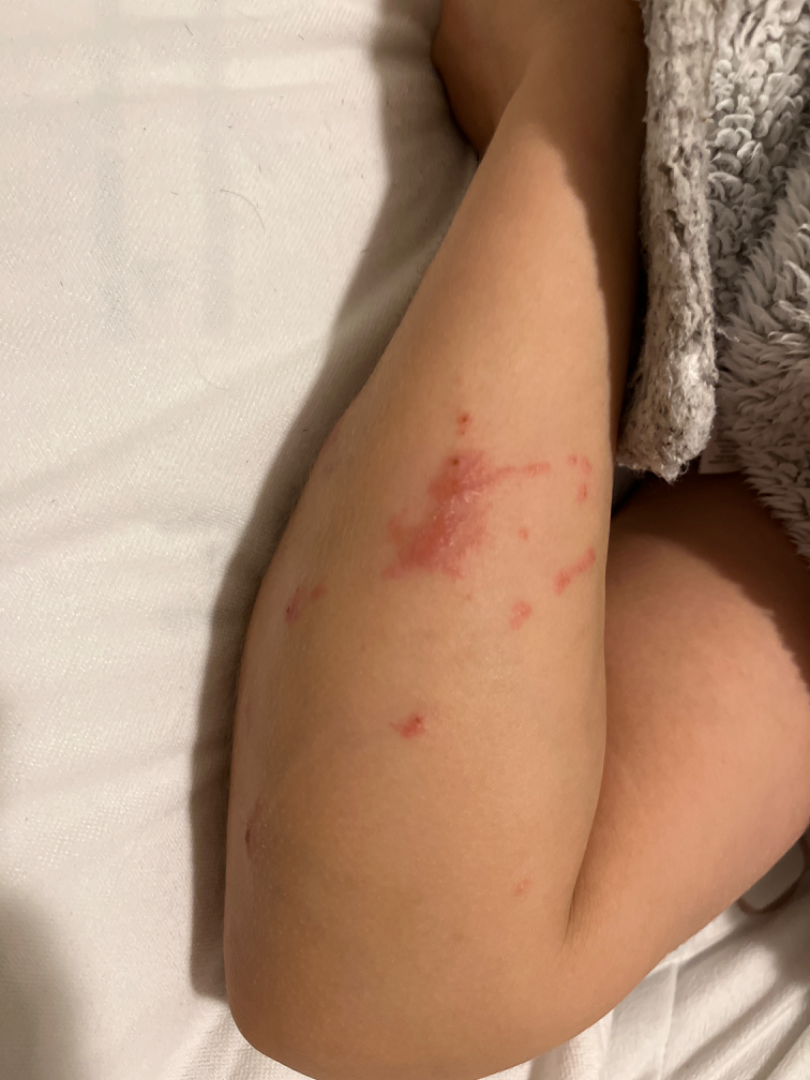The case was difficult to assess from the available photograph.
Texture is reported as raised or bumpy and fluid-filled.
No relevant systemic symptoms.
Skin tone: self-reported Fitzpatrick phototype IV; human graders estimated Monk Skin Tone 3 or 4.
The subject is a female aged 18–29.
This image was taken at a distance.
Located on the arm.
The patient considered this a rash.